A dermoscopy image of a single skin lesion: 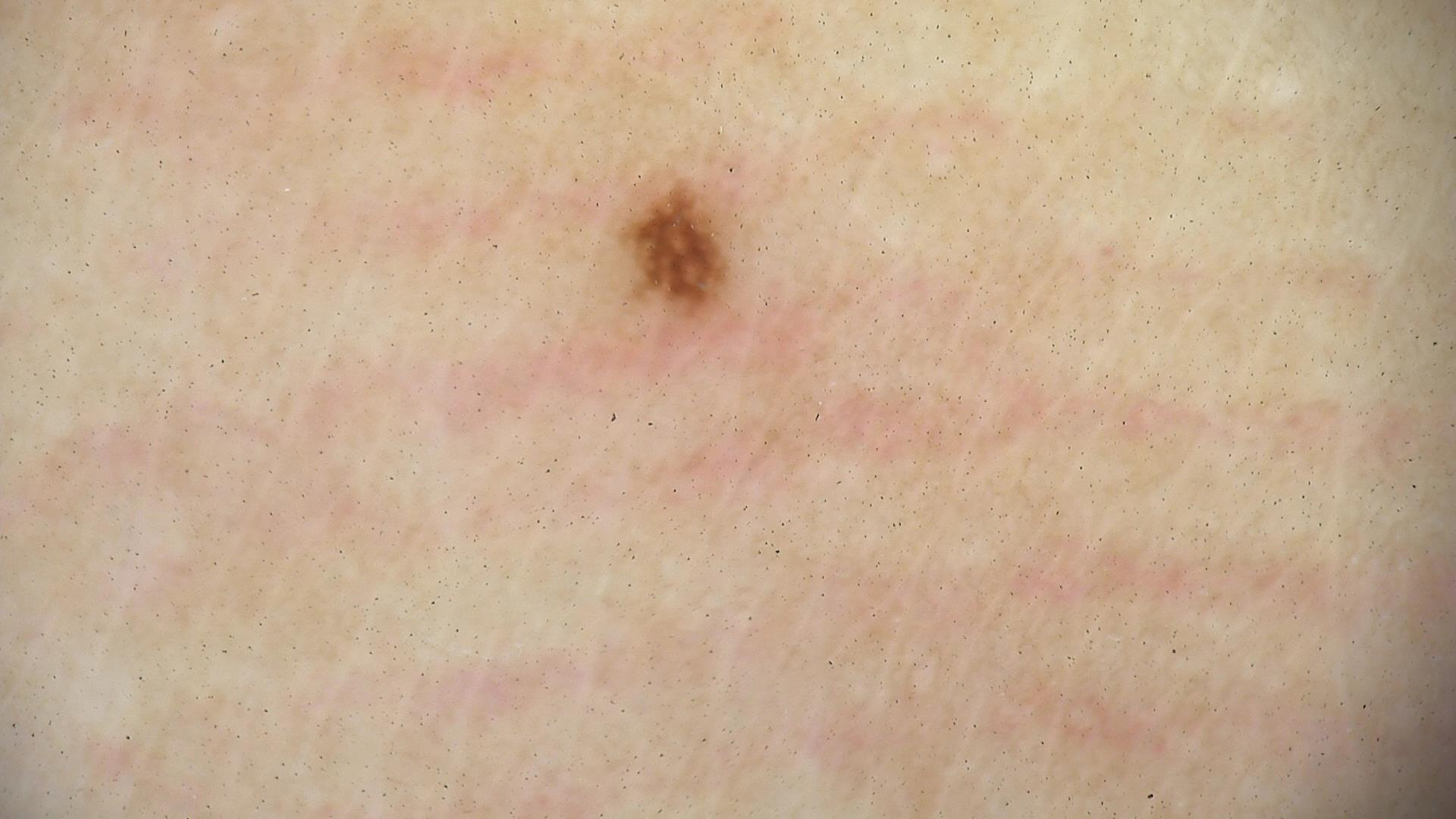  diagnosis:
    name: acral junctional nevus
    code: ajb
    malignancy: benign
    super_class: melanocytic
    confirmation: expert consensus